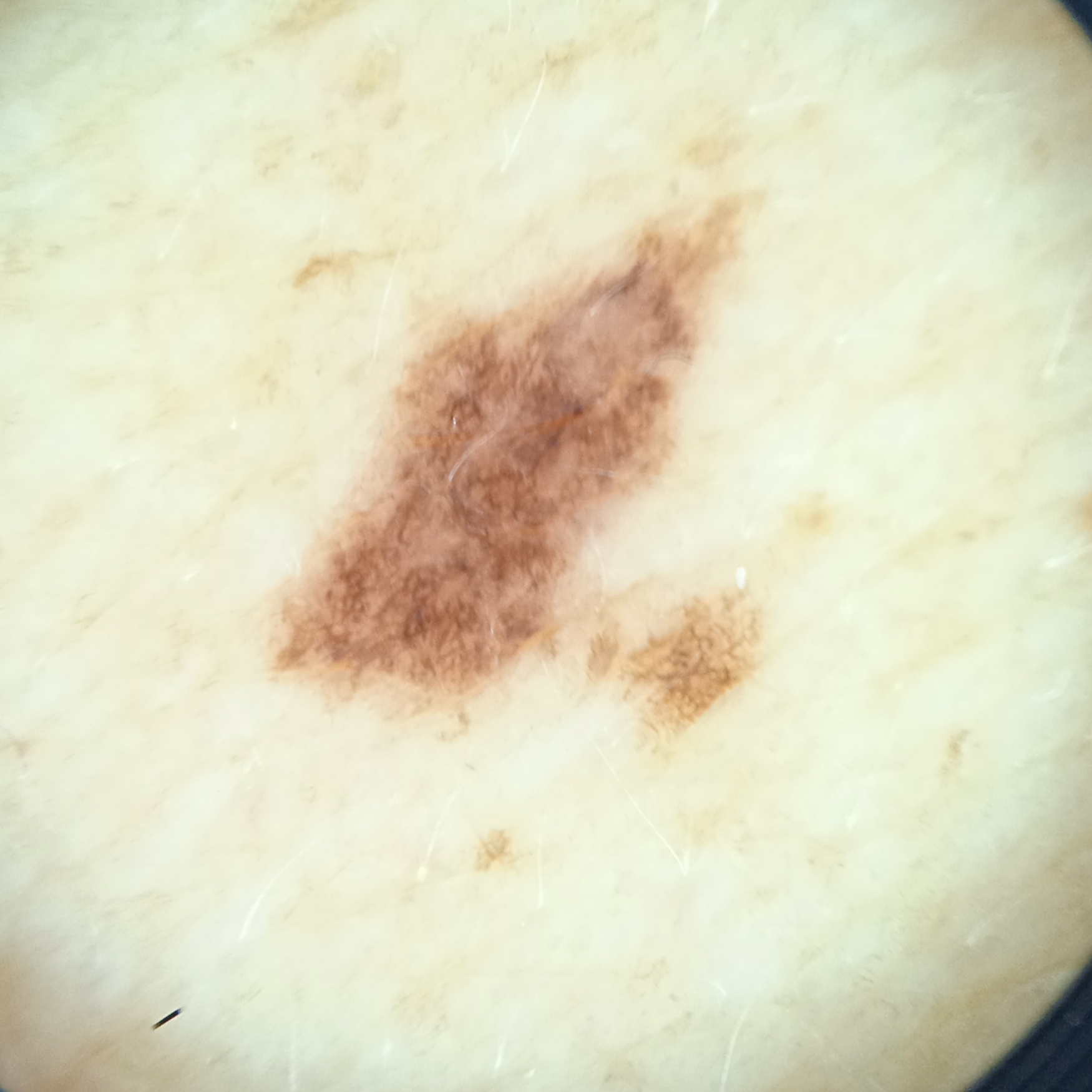- patient: female, 64 years of age
- imaging: dermatoscopic image
- nevus count: a moderate number of melanocytic nevi
- sun reaction: skin tans without first burning
- relevant history: a personal history of cancer, a family history of skin cancer
- clinical context: clinical suspicion of melanocytic nevus
- body site: the back
- size: 8.3 mm
- diagnostic label: atypical (dysplastic) nevus — biopsy-proven